The patient reports enlargement, itching and bothersome appearance · associated systemic symptoms include shortness of breath, joint pain, fatigue and fever · present for three to twelve months · the patient considered this a rash · located on the front of the torso, leg and back of the torso · female contributor, age 18–29 · this is a close-up image — 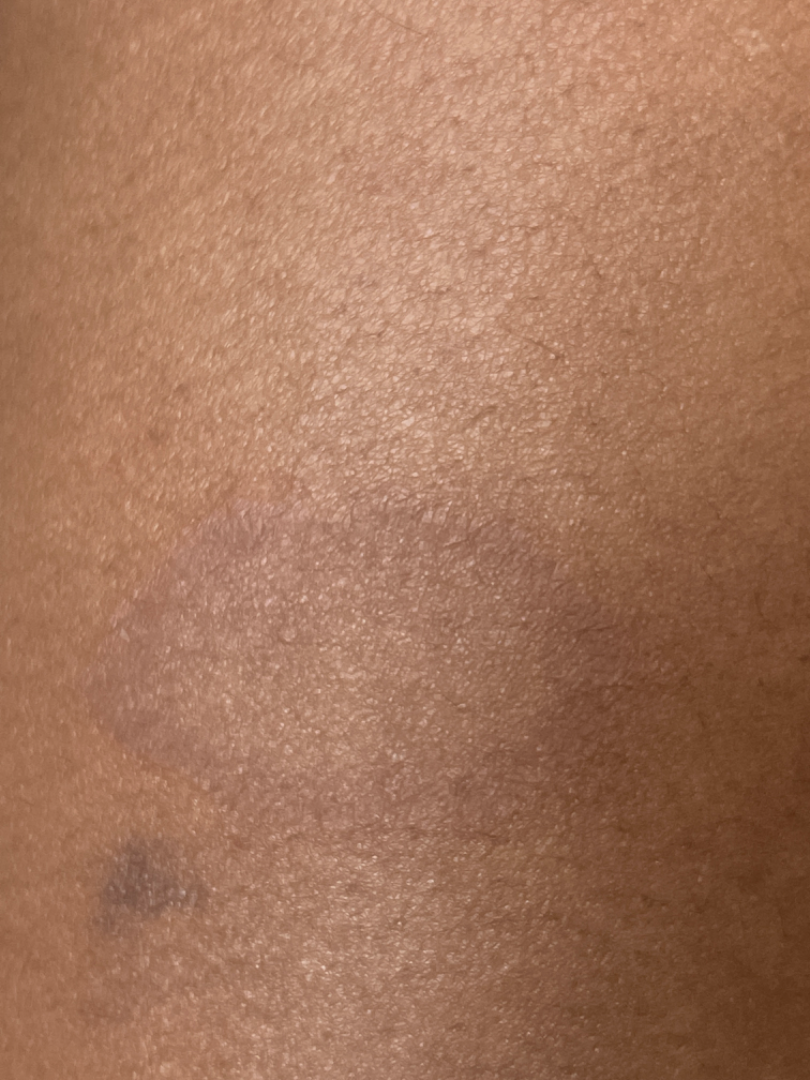<summary>
  <assessment>could not be assessed</assessment>
</summary>